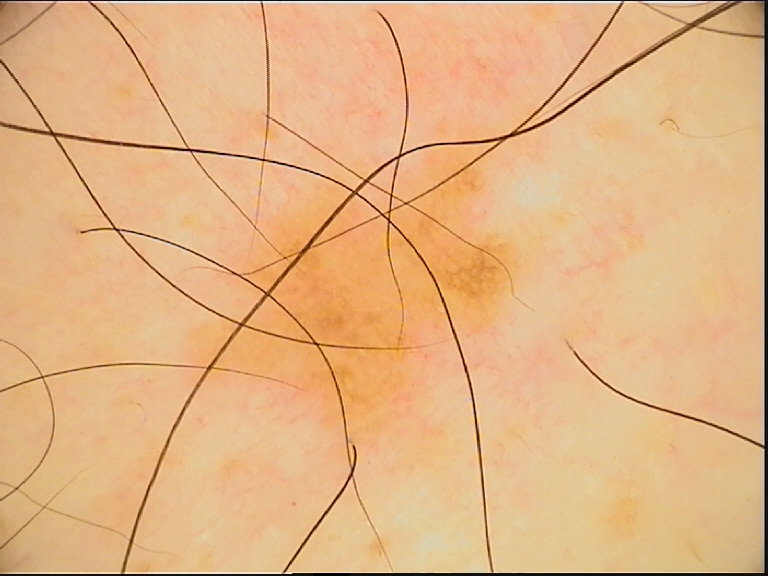A dermoscopy image of a single skin lesion. Classified as a benign lesion — a dysplastic junctional nevus.